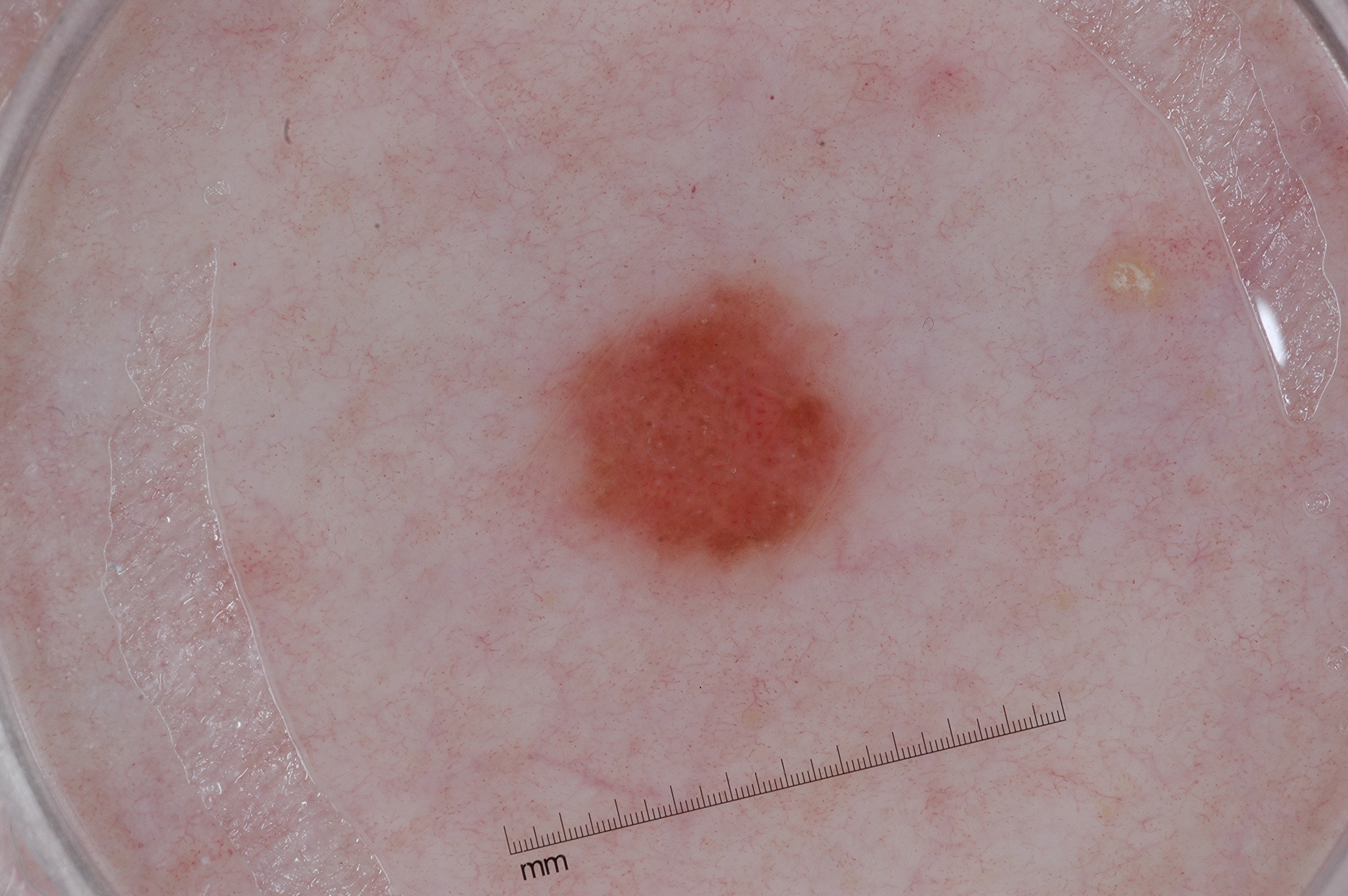Q: What kind of image is this?
A: dermoscopy of a skin lesion
Q: Who is the patient?
A: female, aged approximately 65
Q: What does dermoscopy show?
A: milia-like cysts and negative network
Q: Lesion extent?
A: ~7% of the field
Q: Where is the lesion in the image?
A: left=527, top=273, right=874, bottom=588
Q: What did the assessment conclude?
A: a melanocytic nevus